A dermoscopy image of a single skin lesion.
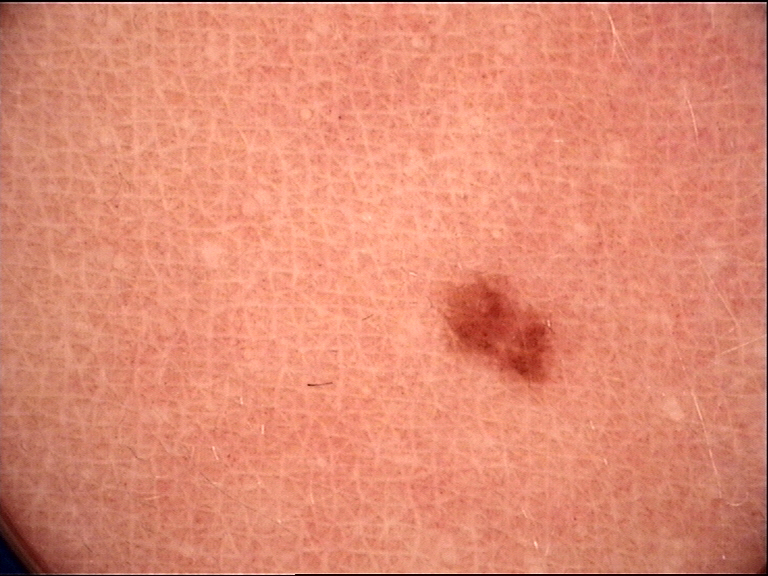Findings:
– class — dysplastic junctional nevus (expert consensus)